Male subject, age 18–29; the lesion involves the front of the torso, arm and back of the torso; this image was taken at a distance: 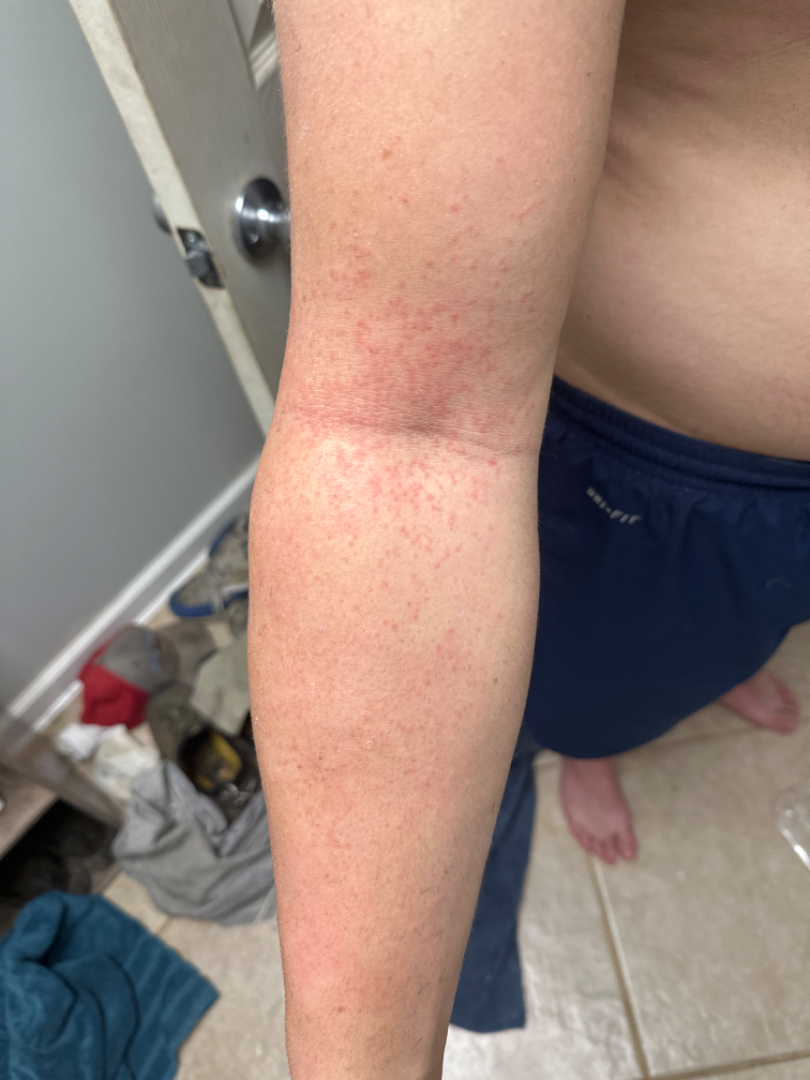skin tone = Fitzpatrick I; patient describes the issue as = a rash; lesion symptoms = bothersome appearance, itching and pain; lesion texture = rough or flaky and flat; symptom duration = about one day; diagnostic considerations = reviewed remotely by one dermatologist: Eczema, Hypersensitivity and Allergic Contact Dermatitis were each considered, in no particular order.